A dermoscopic image of a skin lesion — 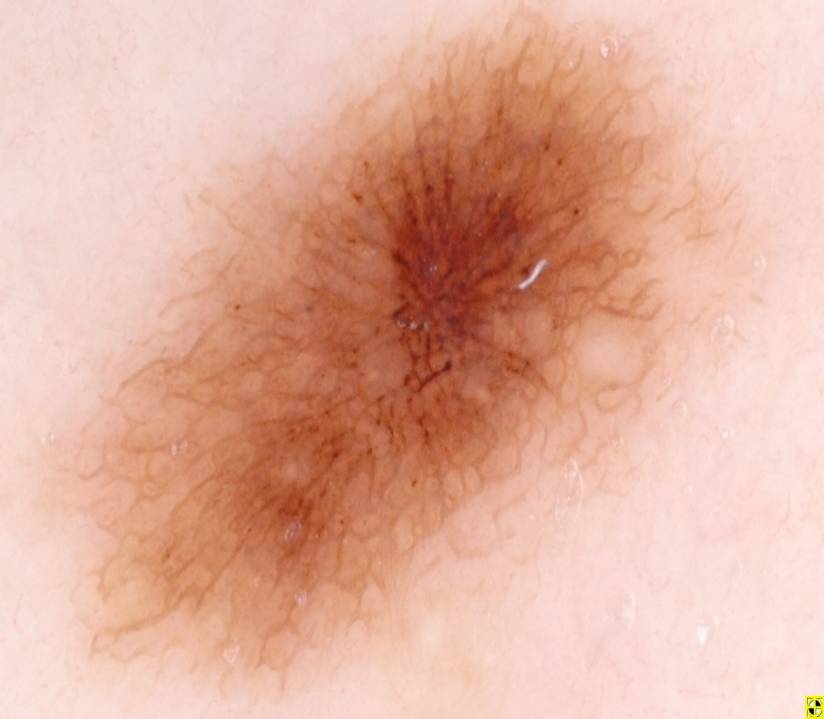On dermoscopy, the lesion shows pigment network and globules; no streaks, negative network, or milia-like cysts. As (left, top, right, bottom), the lesion's extent is [31,0,756,700]. Expert review diagnosed this as a melanocytic nevus.